A dermoscopic photograph of a skin lesion.
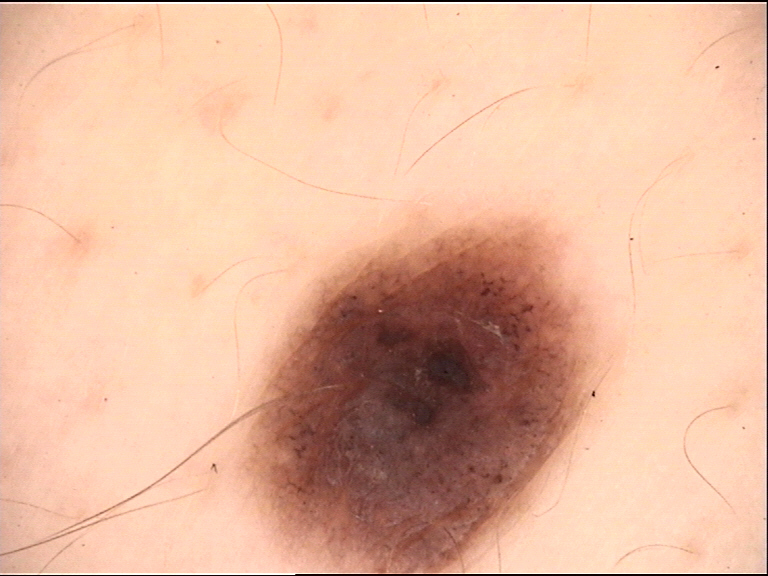Q: What kind of lesion is this?
A: banal
Q: What was the diagnostic impression?
A: compound nevus (expert consensus)